A clinical photo of a skin lesion taken with a smartphone:
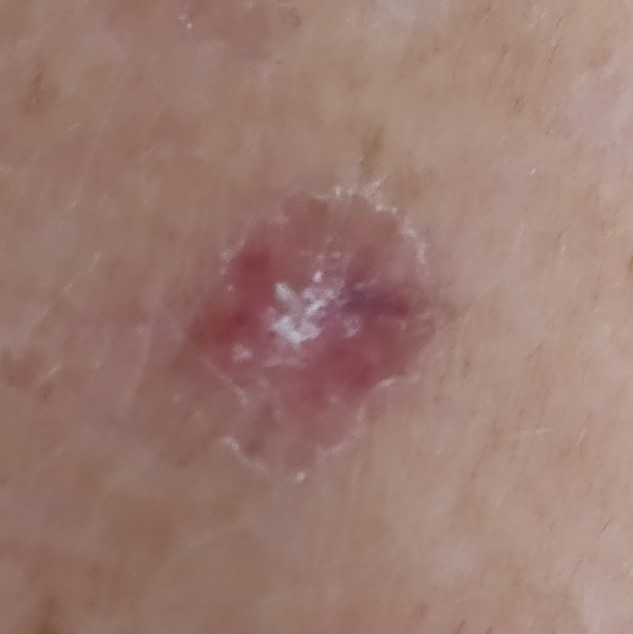The lesion was found on a forearm.
Per patient report, the lesion itches and is elevated.
The consensus clinical diagnosis was an actinic keratosis.